A dermoscopic image of a skin lesion · a male subject, roughly 60 years of age.
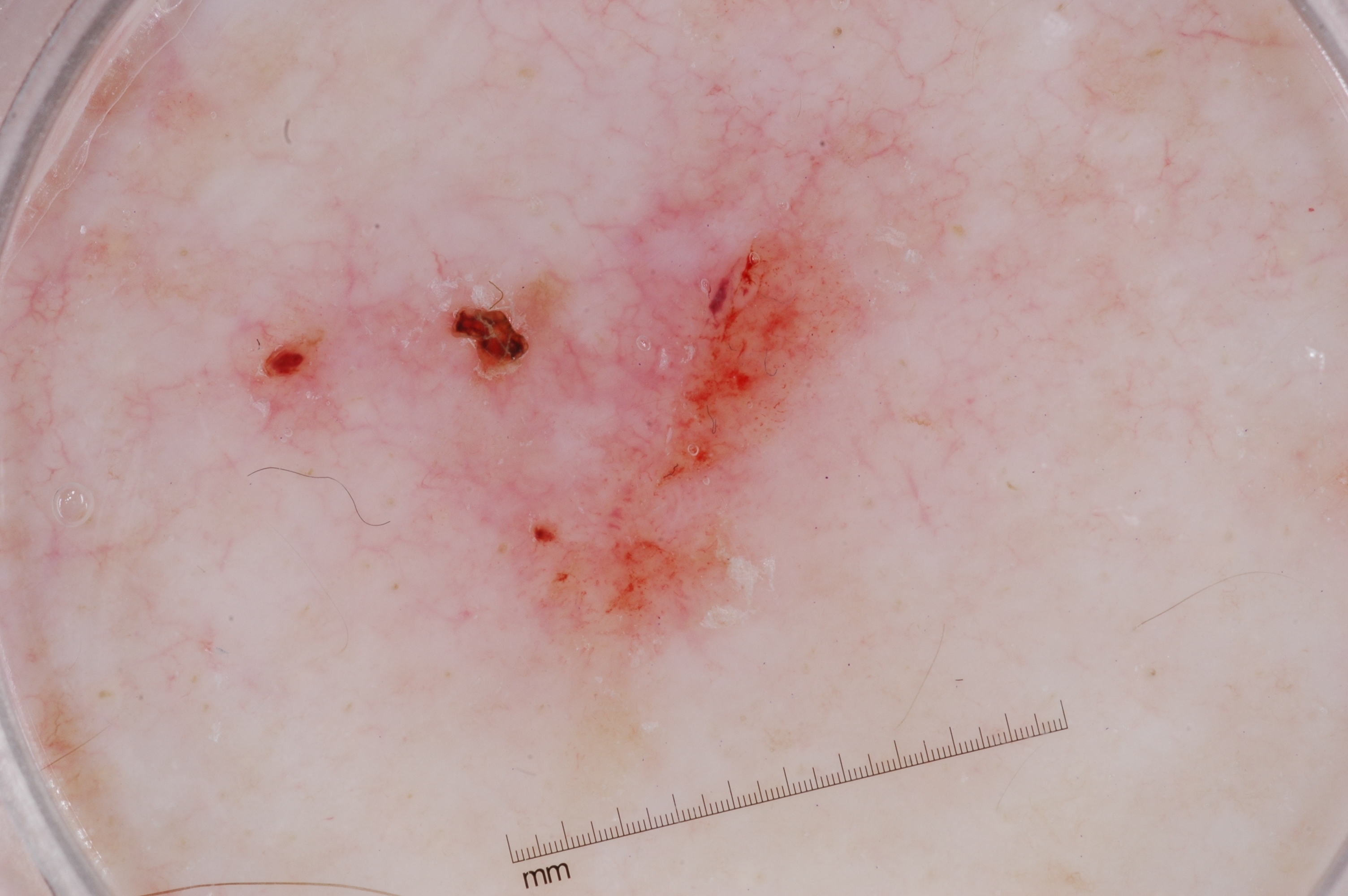Dermoscopic examination shows no pigment network, milia-like cysts, negative network, or streaks.
The lesion takes up about 15% of the image.
Lesion location: <bbox>253, 119, 895, 700</bbox>.
The clinical diagnosis was a seborrheic keratosis.